Close-up view · the back of the torso, front of the torso, arm and head or neck are involved.
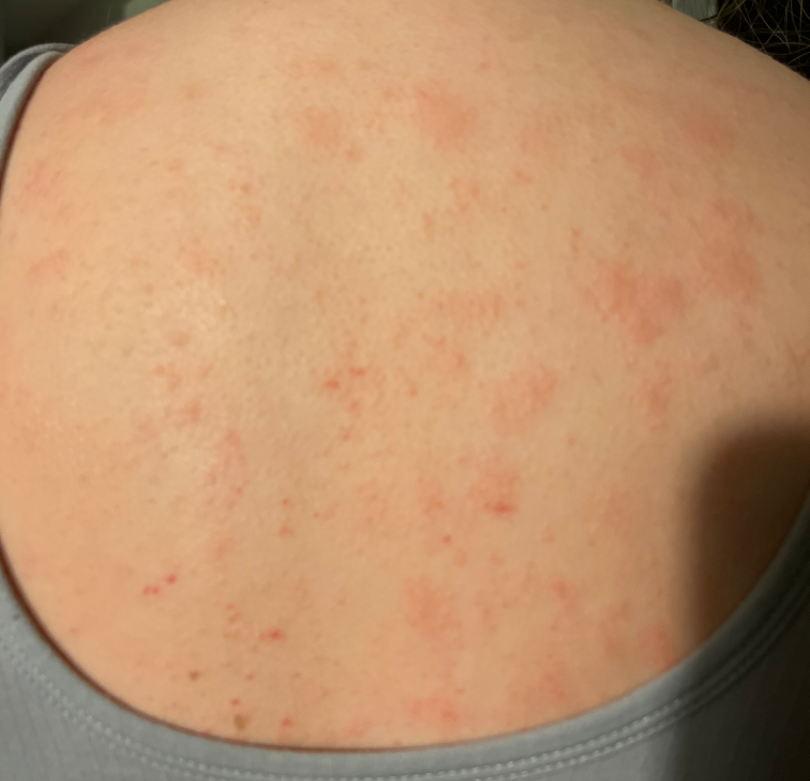Skin tone: Fitzpatrick skin type II. Reported duration is one to four weeks. The lesion is described as raised or bumpy. The patient considered this a rash. Eczema (weight 0.54); Drug Rash (weight 0.23); Inflicted skin lesions (weight 0.23).